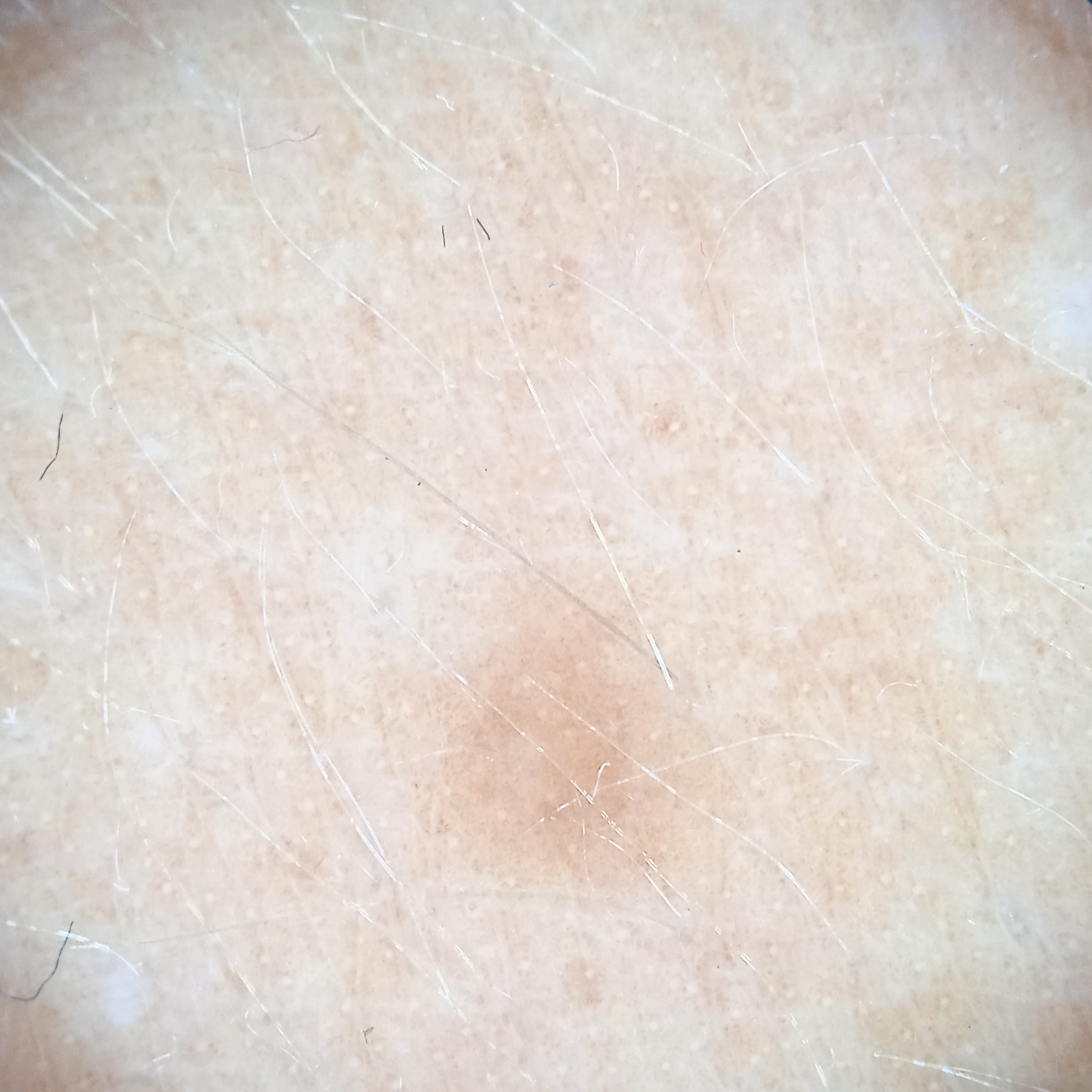The lesion was left diagnostically undetermined on review. The patient describes having a moderate number of moles.
Imaged for a research study, with no referral diagnosis recorded.
The lesion is on the back.
Measuring roughly 3.5 mm.